Close-up view · the lesion involves the head or neck:
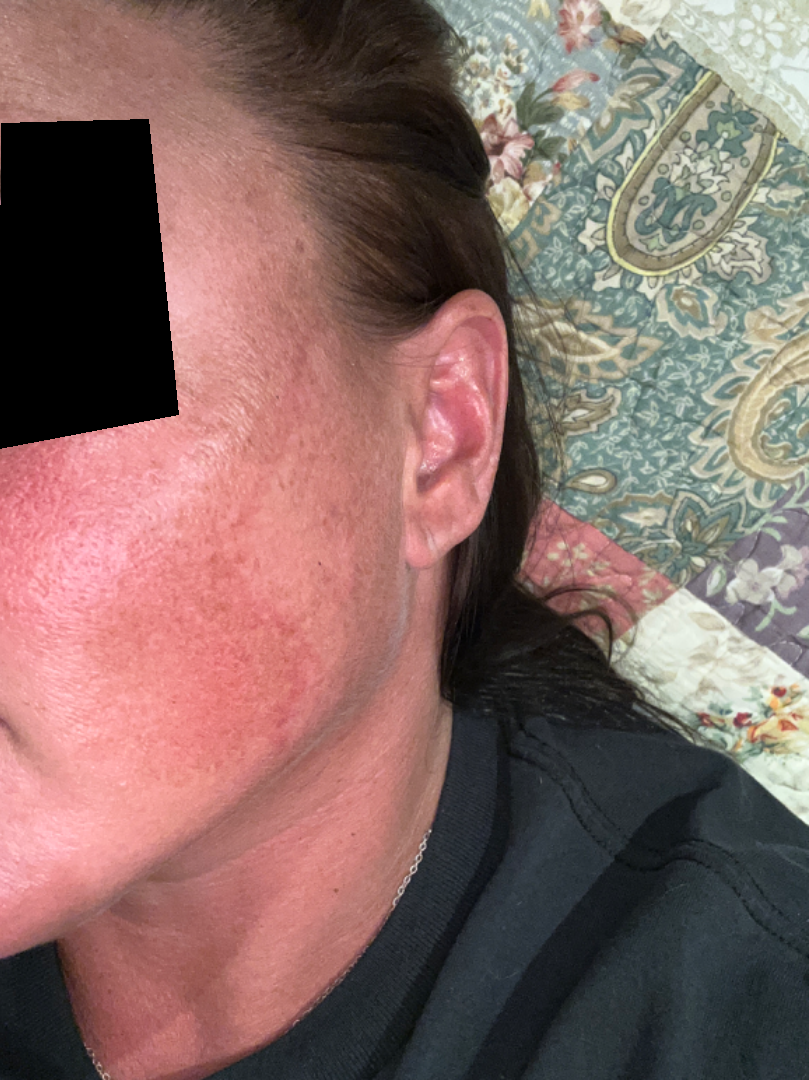Assessment:
The reviewing clinician's impression was: most consistent with Melasma.